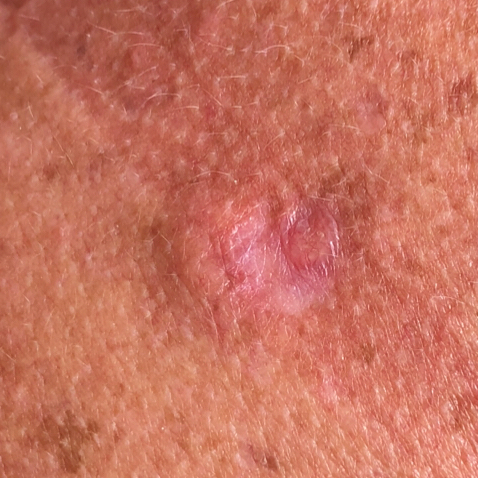modality: smartphone clinical photo; risk factors: alcohol use, tobacco use, prior malignancy (patient or family), prior skin cancer (patient or family), no pesticide exposure; subject: female, in their mid-40s; Fitzpatrick: II; anatomic site: the chest; size: 12x12 mm; patient-reported symptoms: itching, growth, elevation / no pain, no bleeding; pathology: basal cell carcinoma (biopsy-proven).